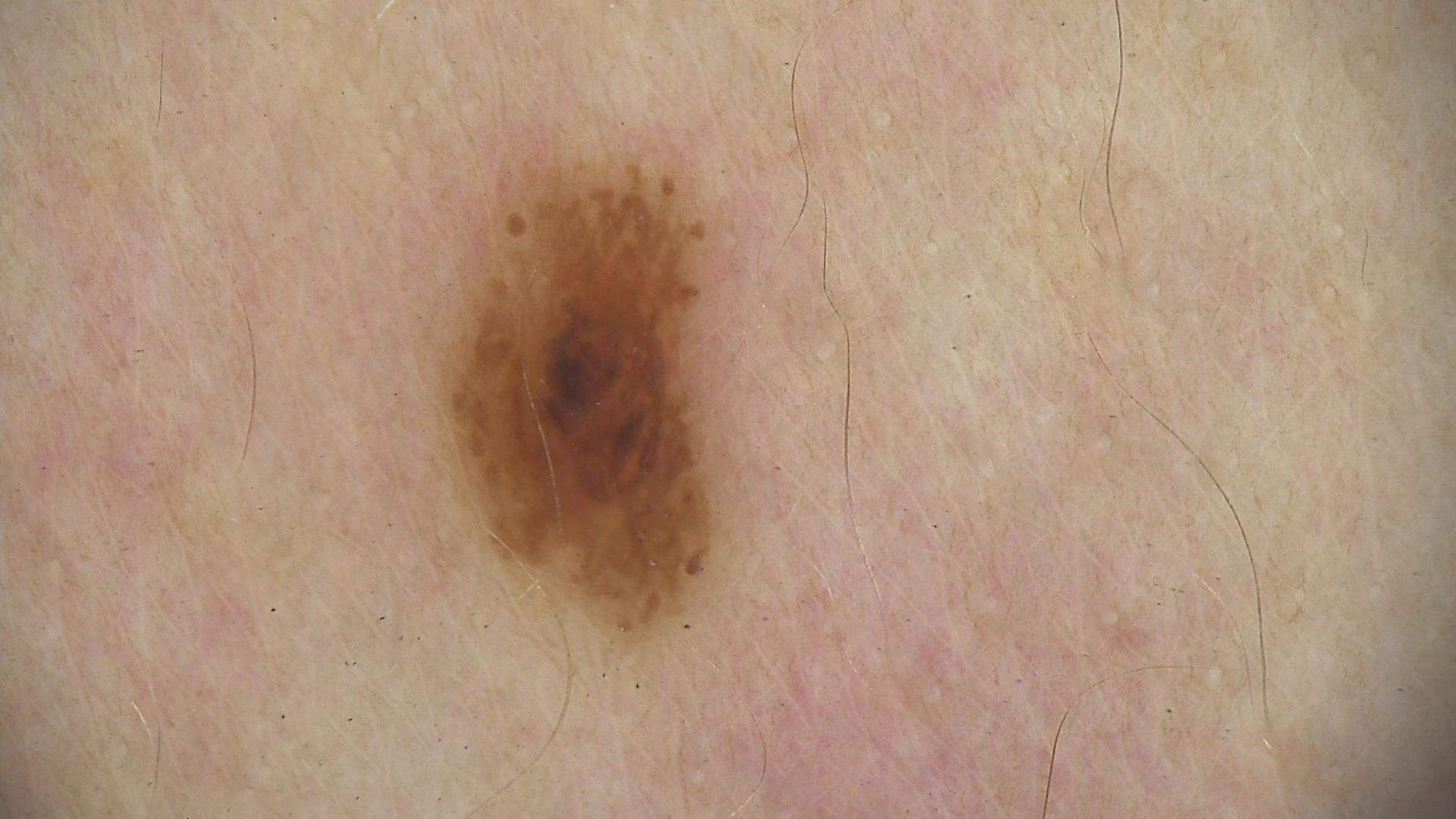Dermoscopy of a skin lesion. The diagnostic label was a dysplastic junctional nevus.